A dermoscopy image of a single skin lesion.
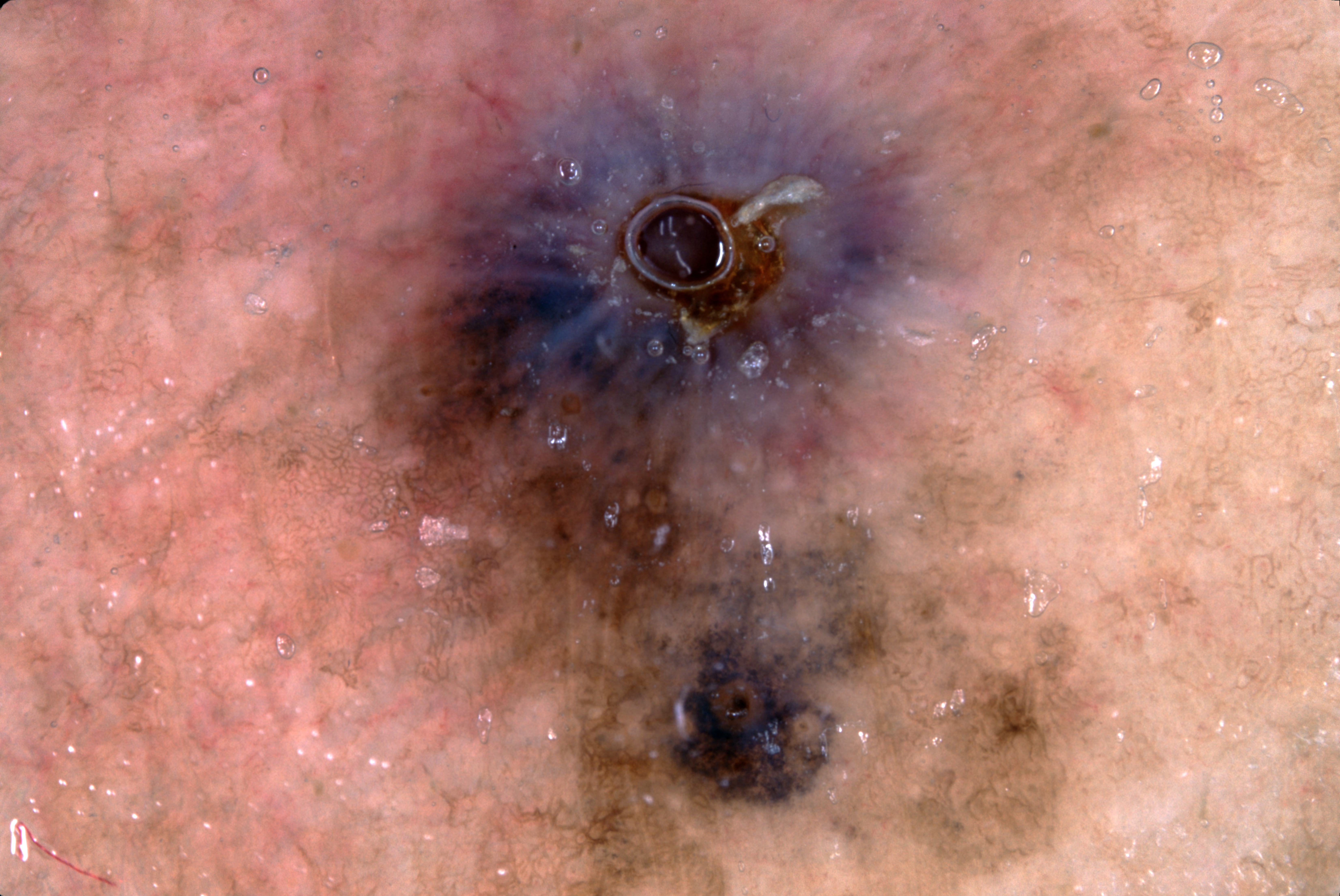lesion bbox=194 0 1154 895 | diagnostic label=a melanoma.